A dermoscopic photograph of a skin lesion:
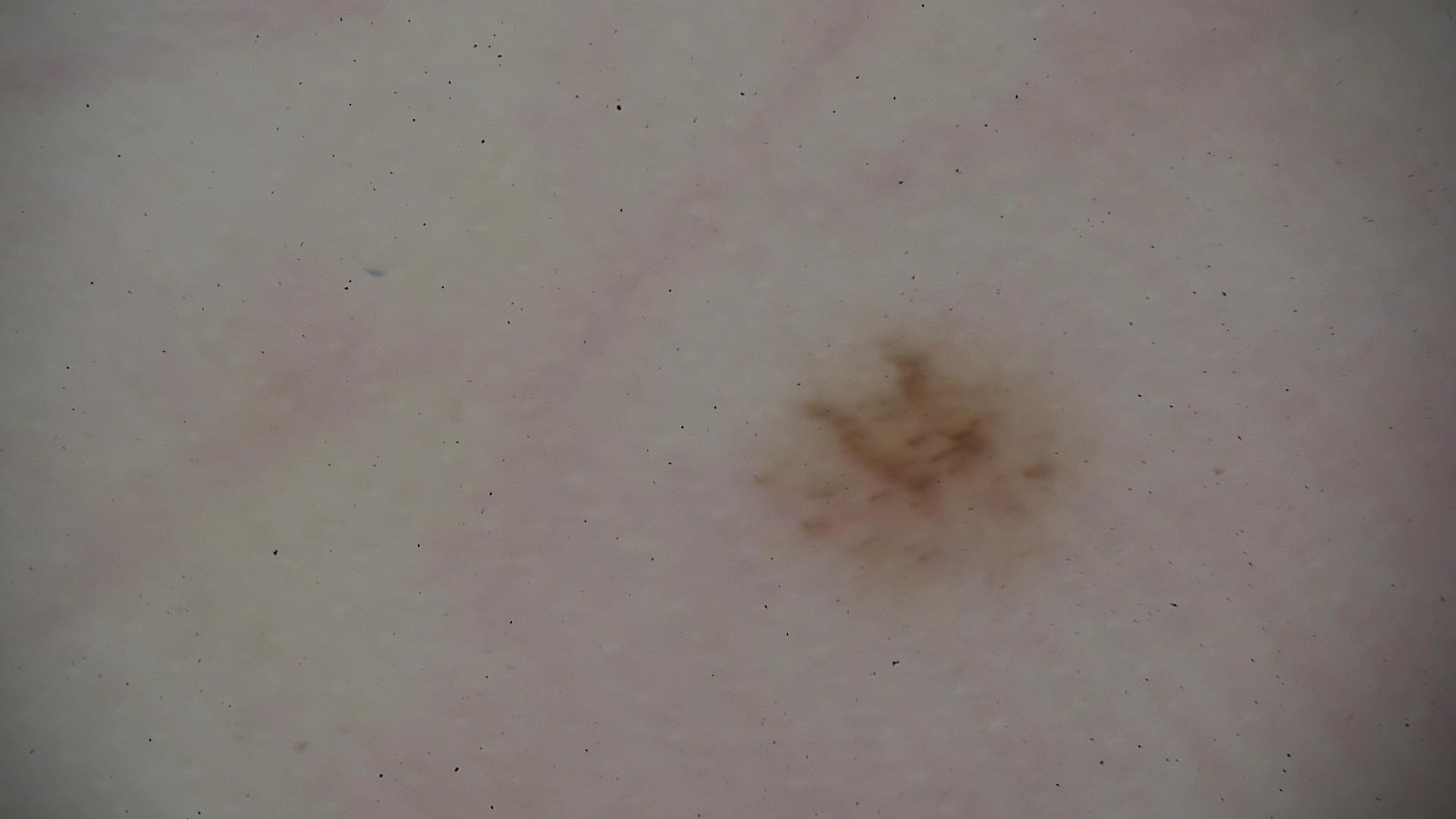Consistent with a benign lesion — an acral dysplastic junctional nevus.